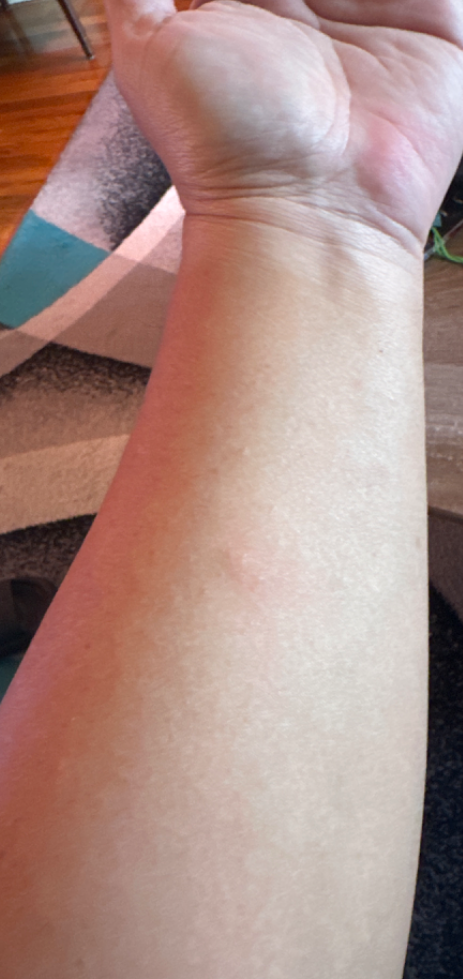| field | value |
|---|---|
| associated systemic symptoms | none reported |
| symptoms | itching and bothersome appearance |
| body site | arm |
| history | about one day |
| contributor | male |
| patient describes the issue as | a rash |
| texture | raised or bumpy |
| framing | at a distance |
| dermatologist impression | Urticaria (33%); Insect Bite (33%); Cyst (33%) |